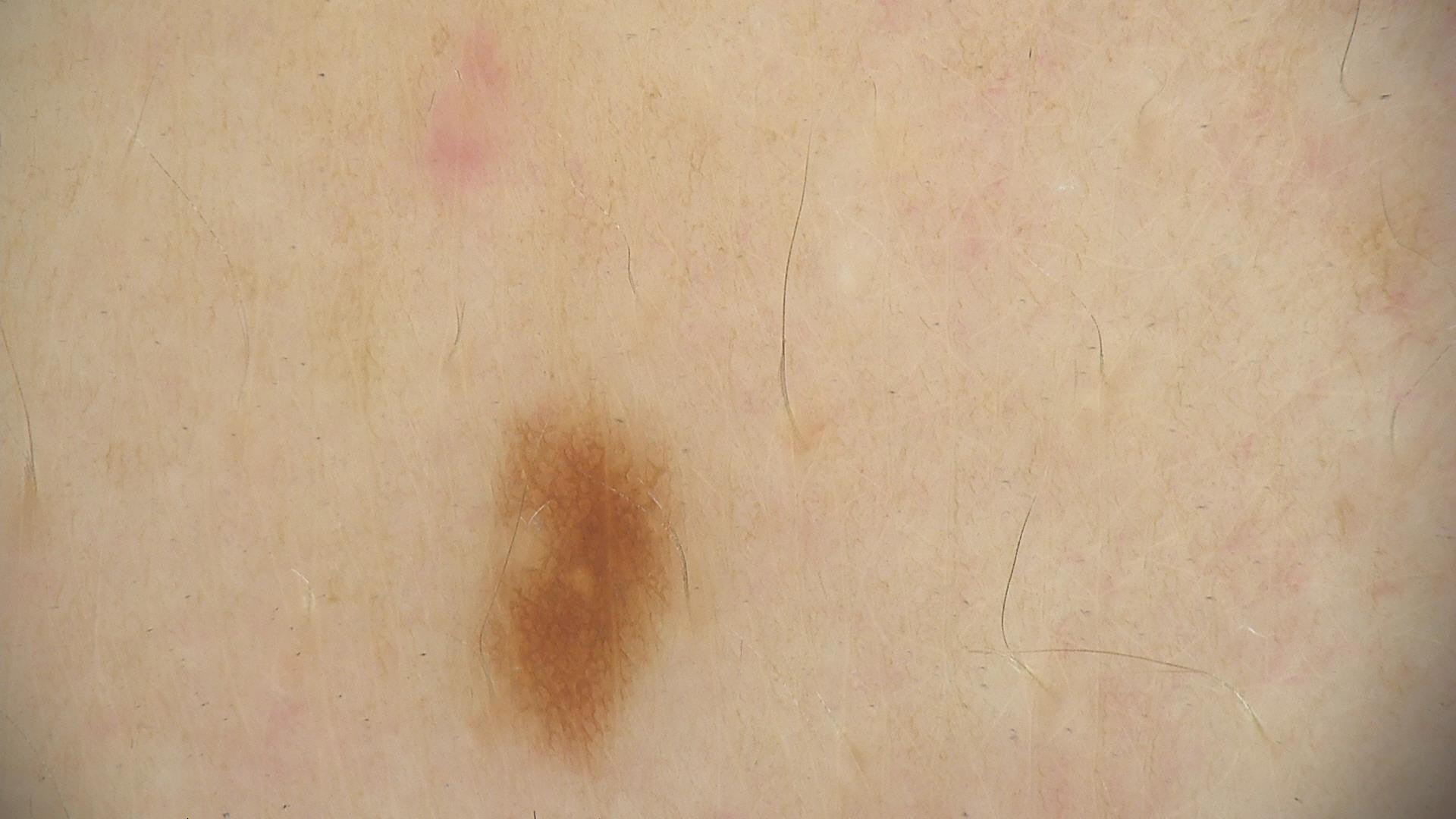A dermoscopy image of a single skin lesion. Diagnosed as a dysplastic junctional nevus.